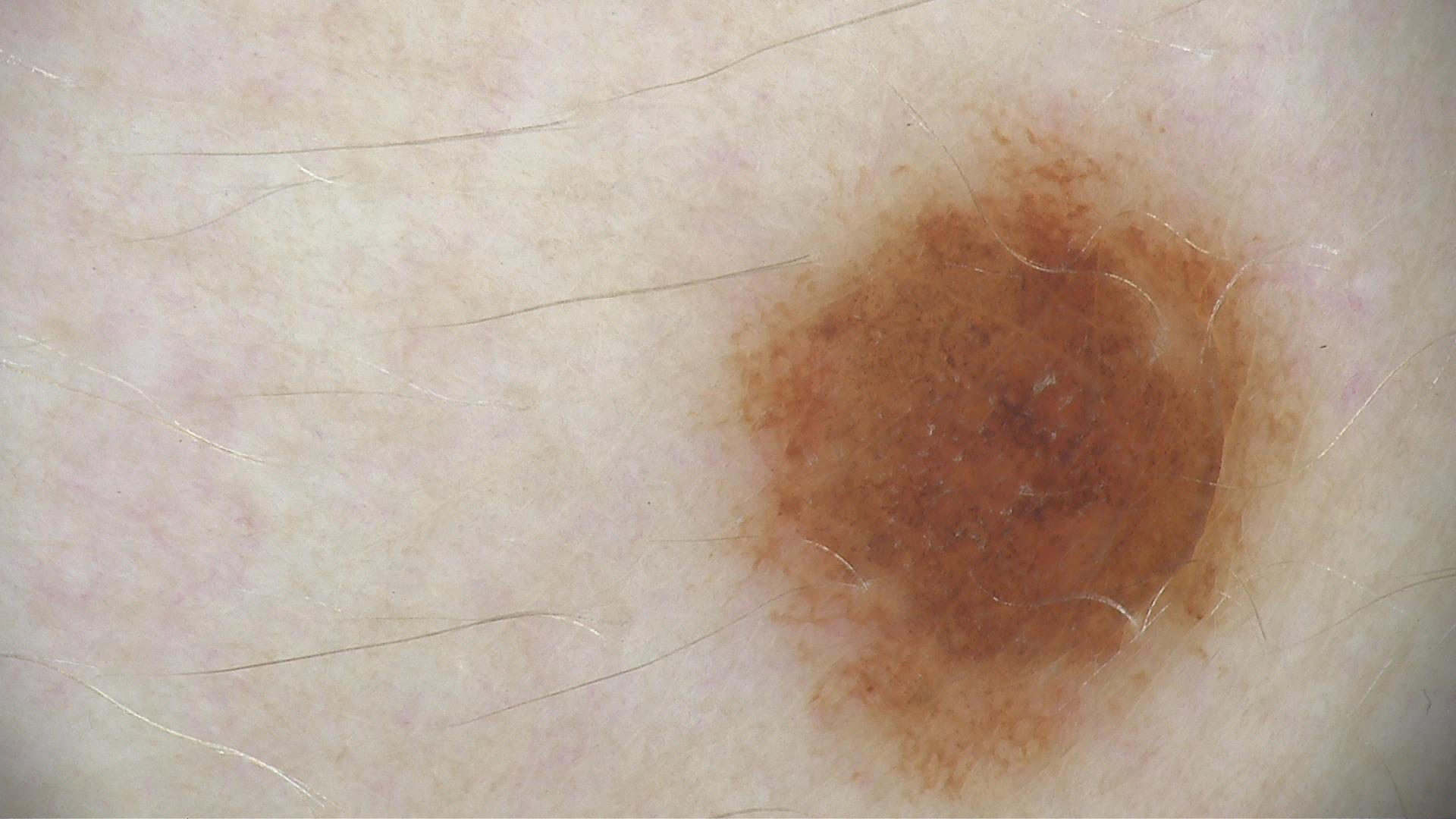image type: dermoscopy; lesion type: banal; label: compound nevus (expert consensus).